Dermoscopy of a skin lesion.
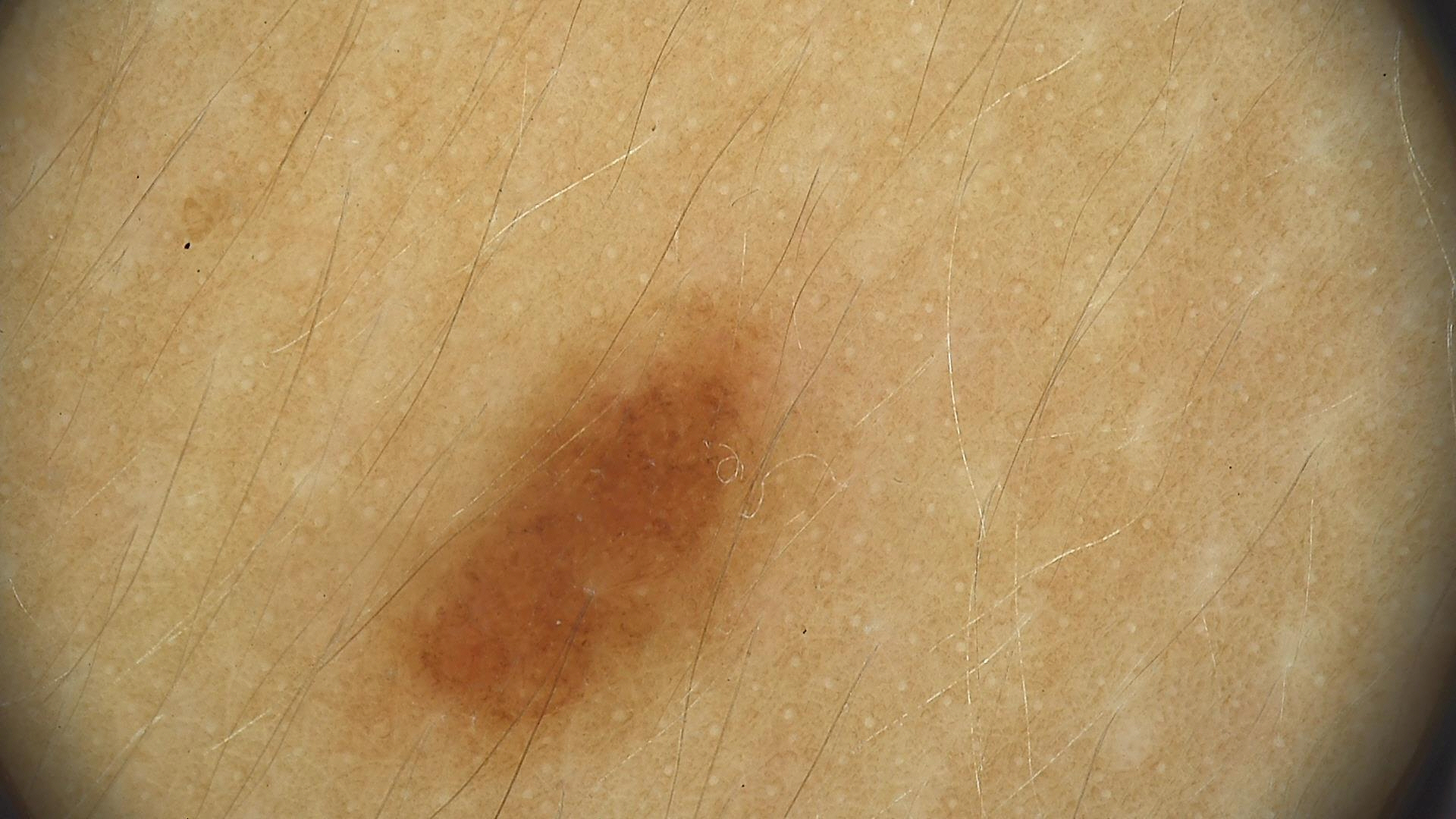Classified as a dysplastic junctional nevus.